A female subject, about 80 years old · a dermoscopic image of a skin lesion: 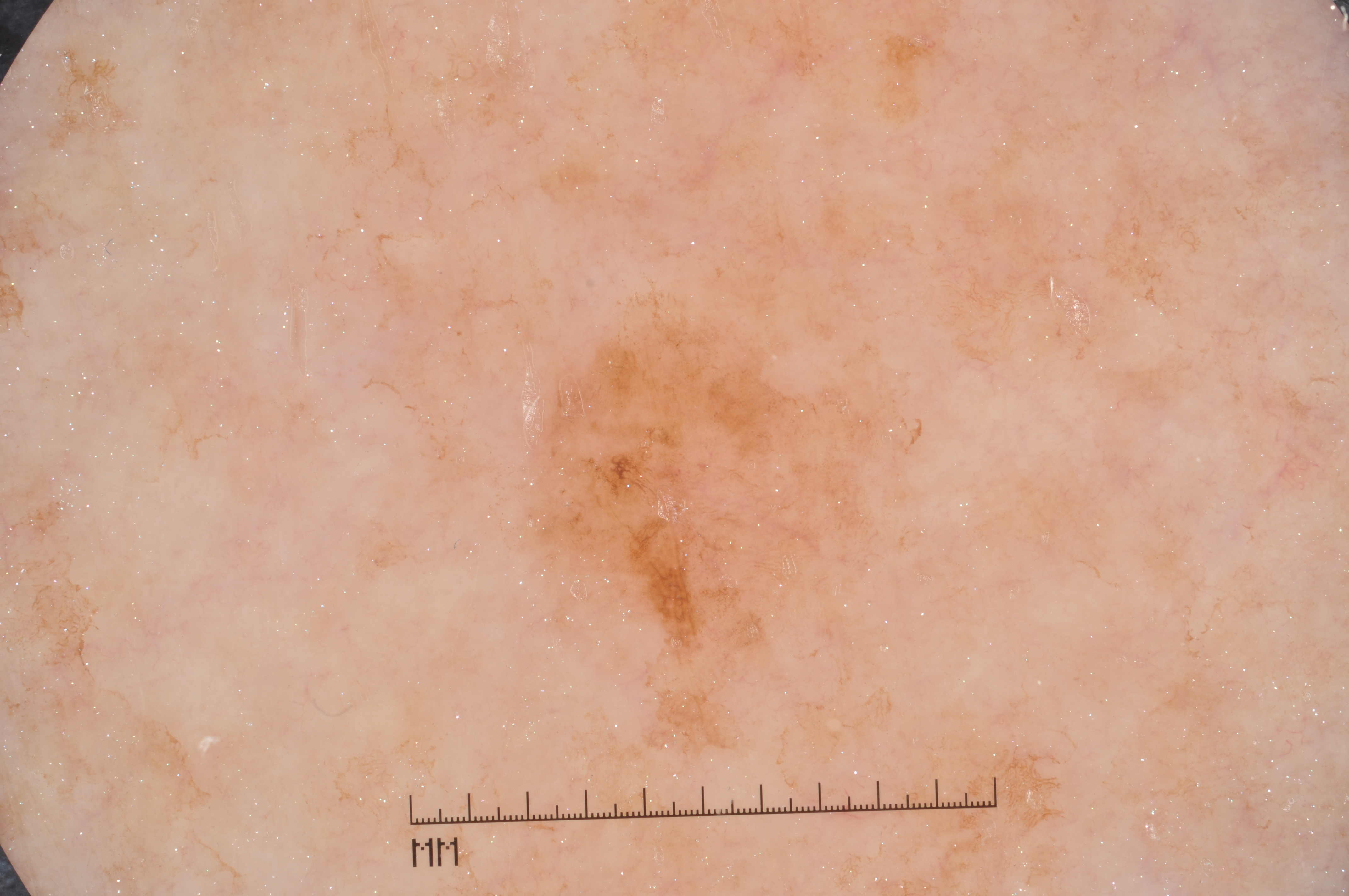extent — ~8% of the field
dermoscopic features — pigment network and milia-like cysts; absent: streaks and negative network
location — left=527, top=309, right=906, bottom=665
diagnosis — a melanoma, a skin cancer